A clinical photograph showing a skin lesion:
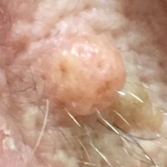Notes:
• body site — the face
• symptoms — elevation / no pain
• diagnosis — squamous cell carcinoma (biopsy-proven)